A close-up photograph: 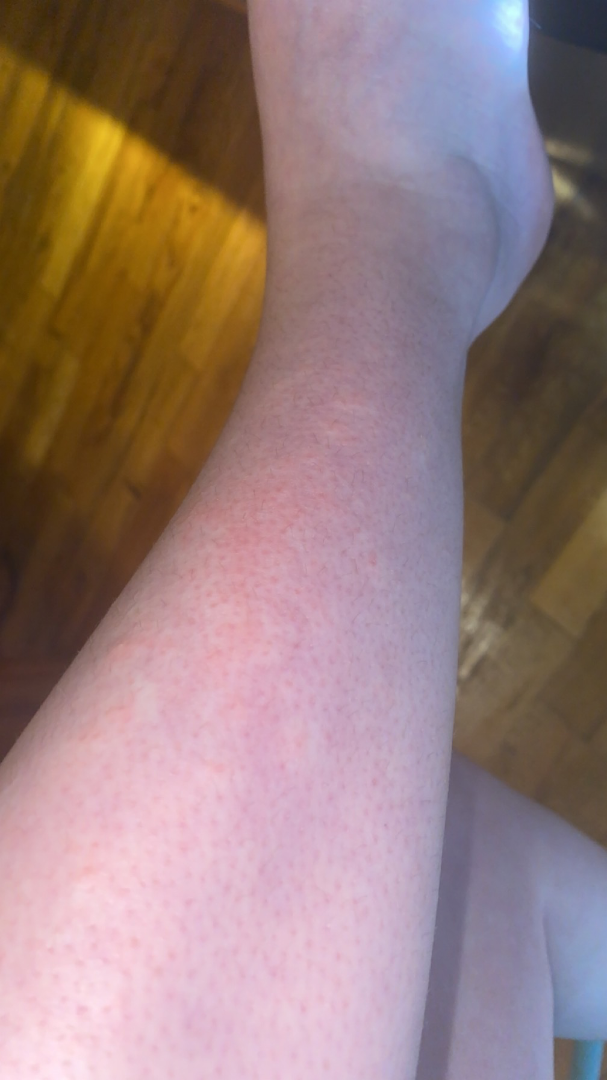The condition could not be reliably identified from the image.